Located on the leg. A close-up photograph — 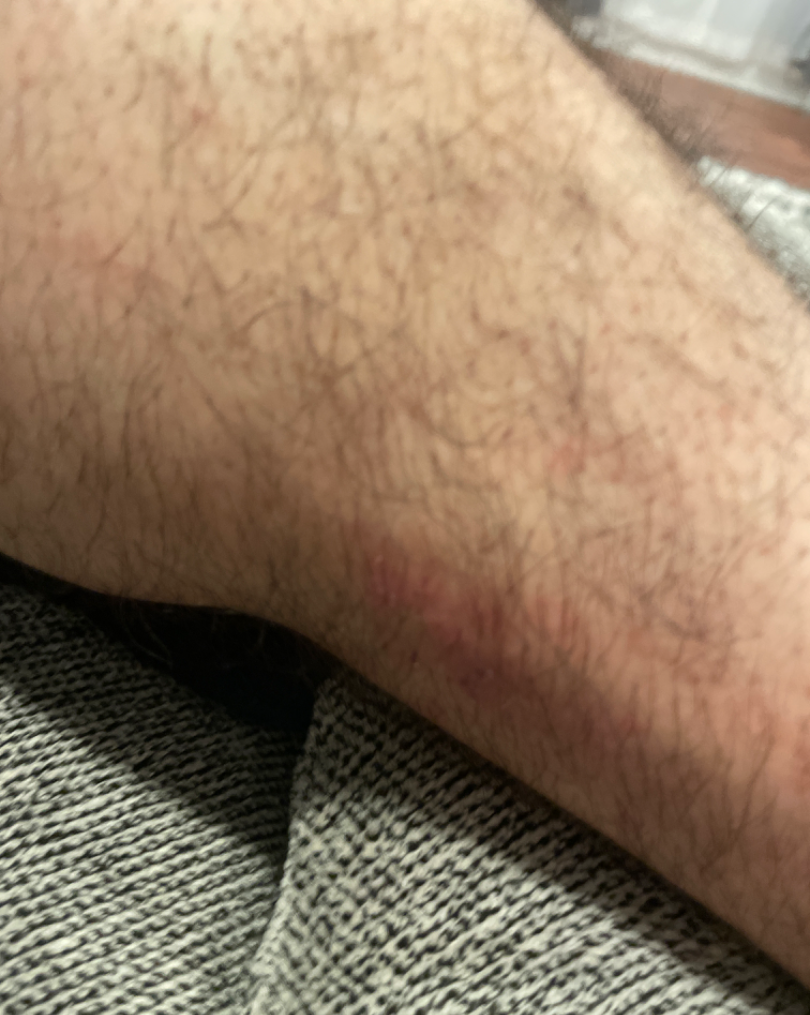The image was not sufficient for the reviewer to characterize the skin condition.